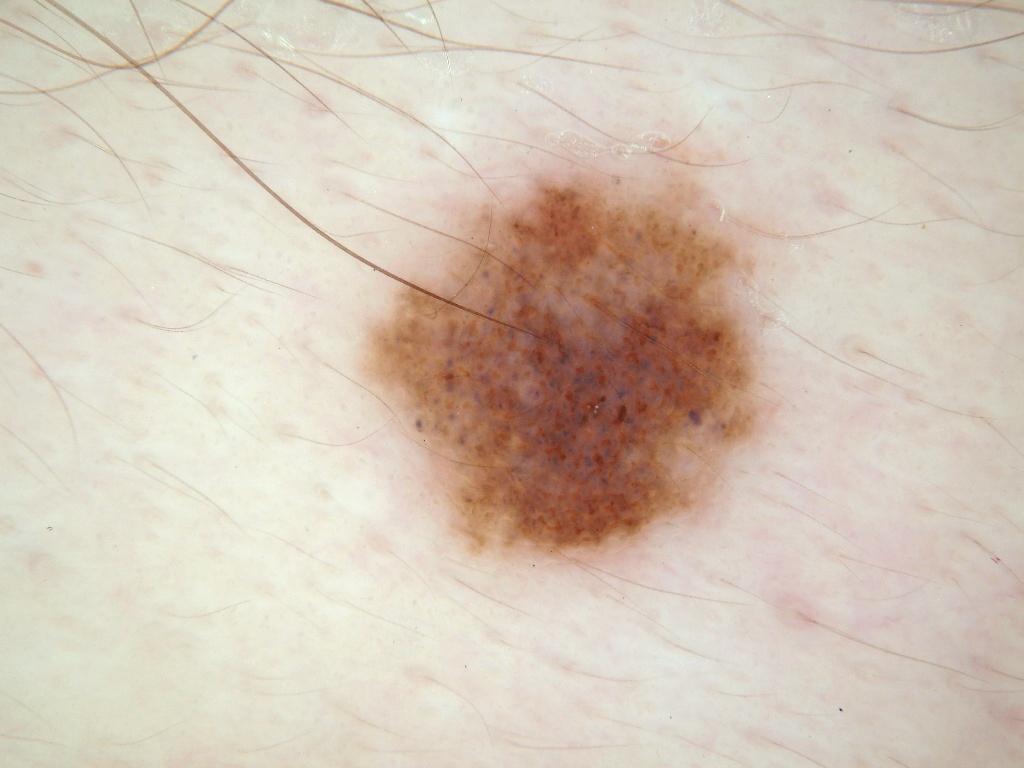A dermoscopy image of a single skin lesion. The lesion is located at left=373, top=173, right=759, bottom=561. Expert review diagnosed this as a melanocytic nevus, a benign lesion.